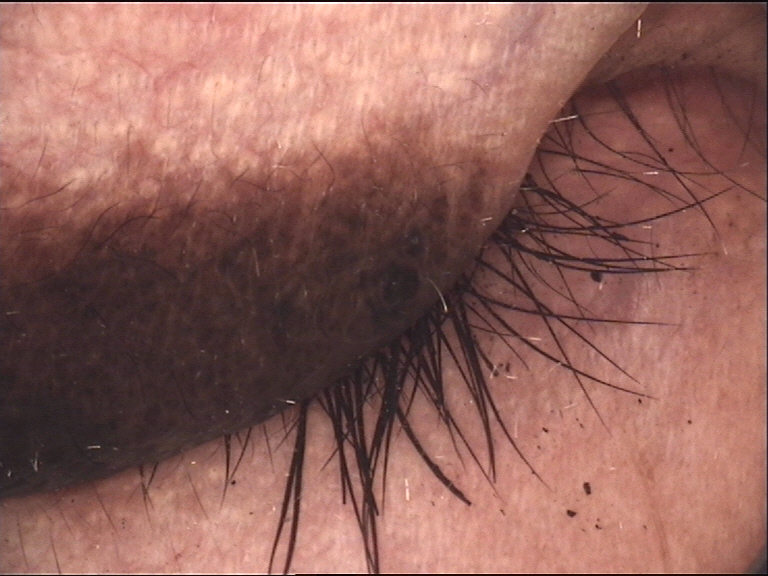{"image": "dermatoscopy", "diagnosis": {"name": "congenital compound nevus", "code": "ccb", "malignancy": "benign", "super_class": "melanocytic", "confirmation": "expert consensus"}}